The arm is involved · this image was taken at a distance:
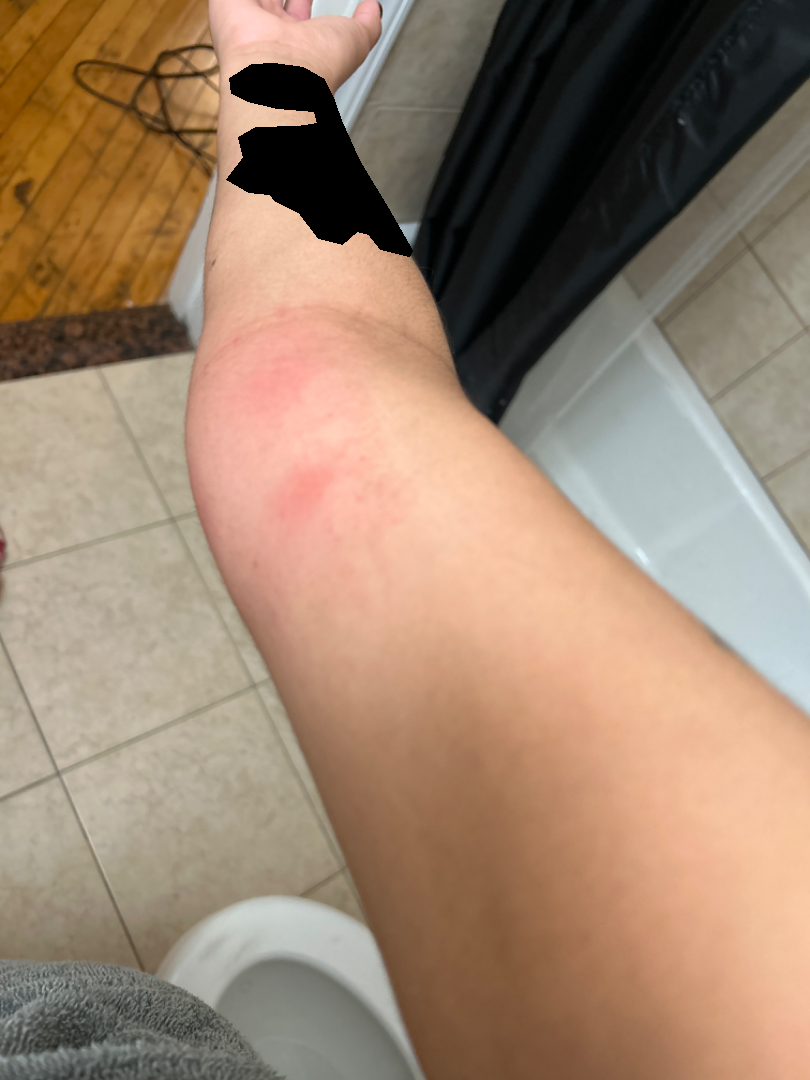Q: How does the patient describe it?
A: a rash
Q: Texture?
A: raised or bumpy
Q: How long has this been present?
A: about one day
Q: What conditions are considered?
A: the leading consideration is Insect Bite